A dermoscopy image of a single skin lesion:
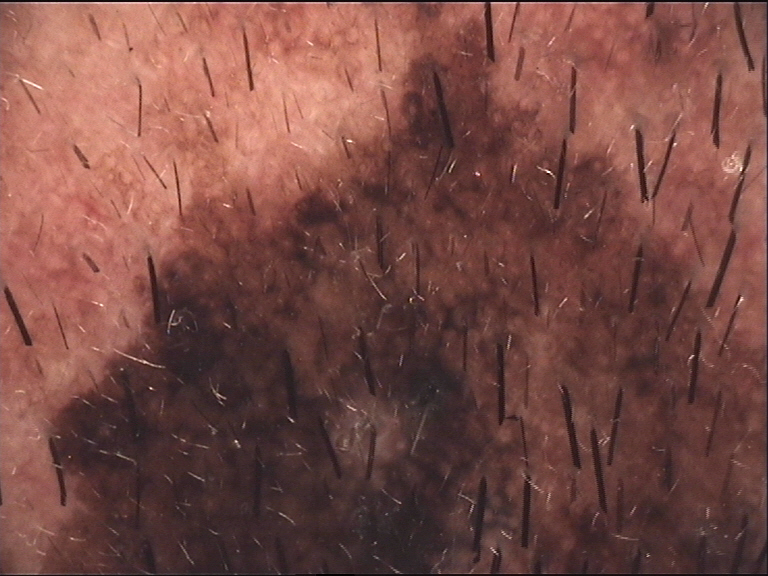Classified as a banal lesion — a congenital compound nevus.